This image was taken at an angle; the leg is involved; the patient is 50–59, female — 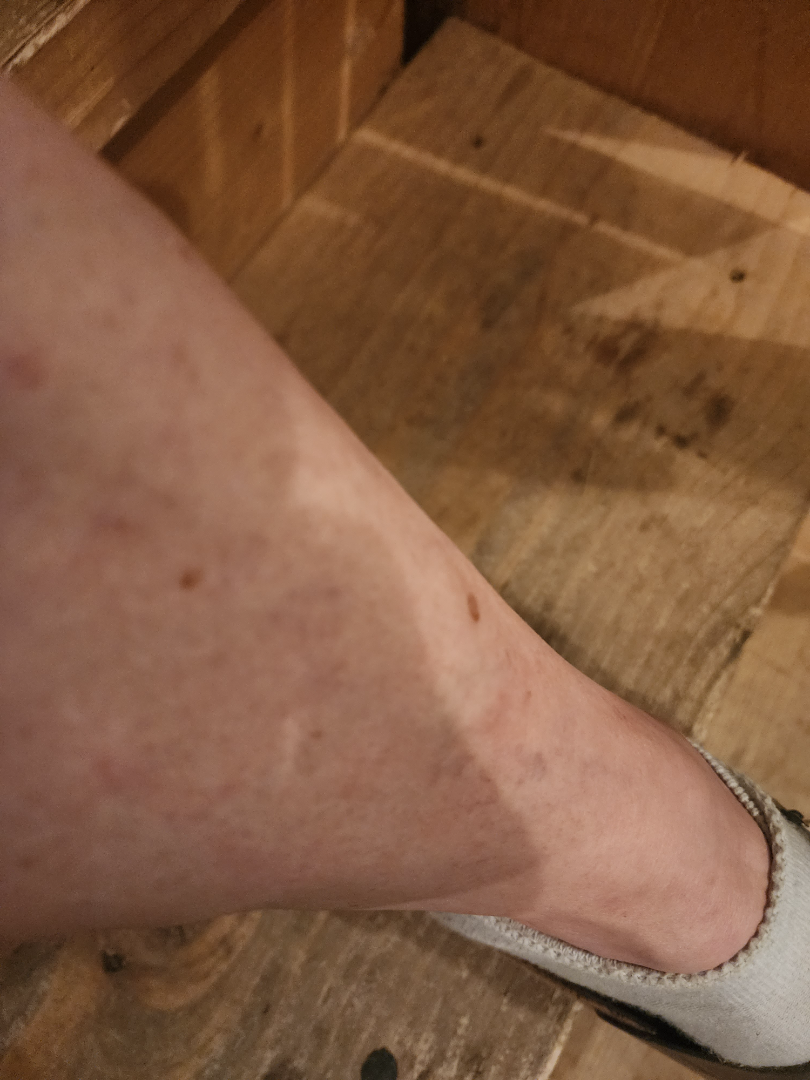Findings:
The reviewer was unable to grade this case for skin condition.